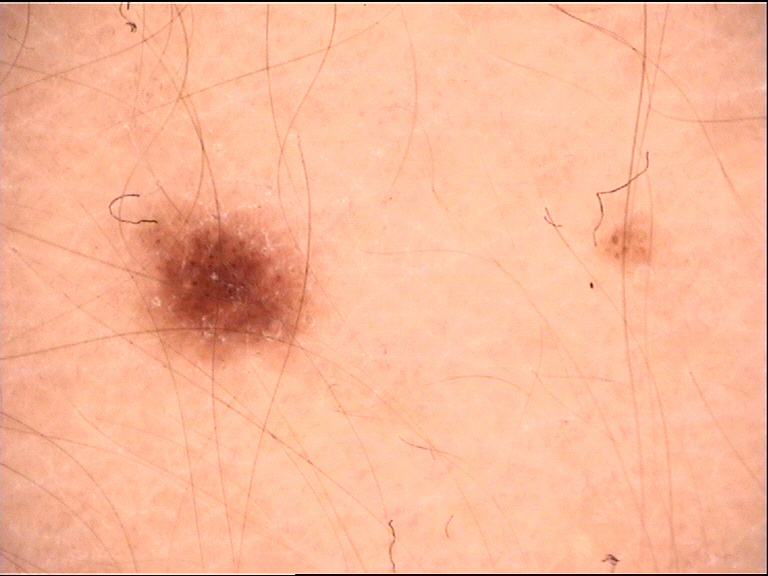Diagnosed as a junctional nevus.